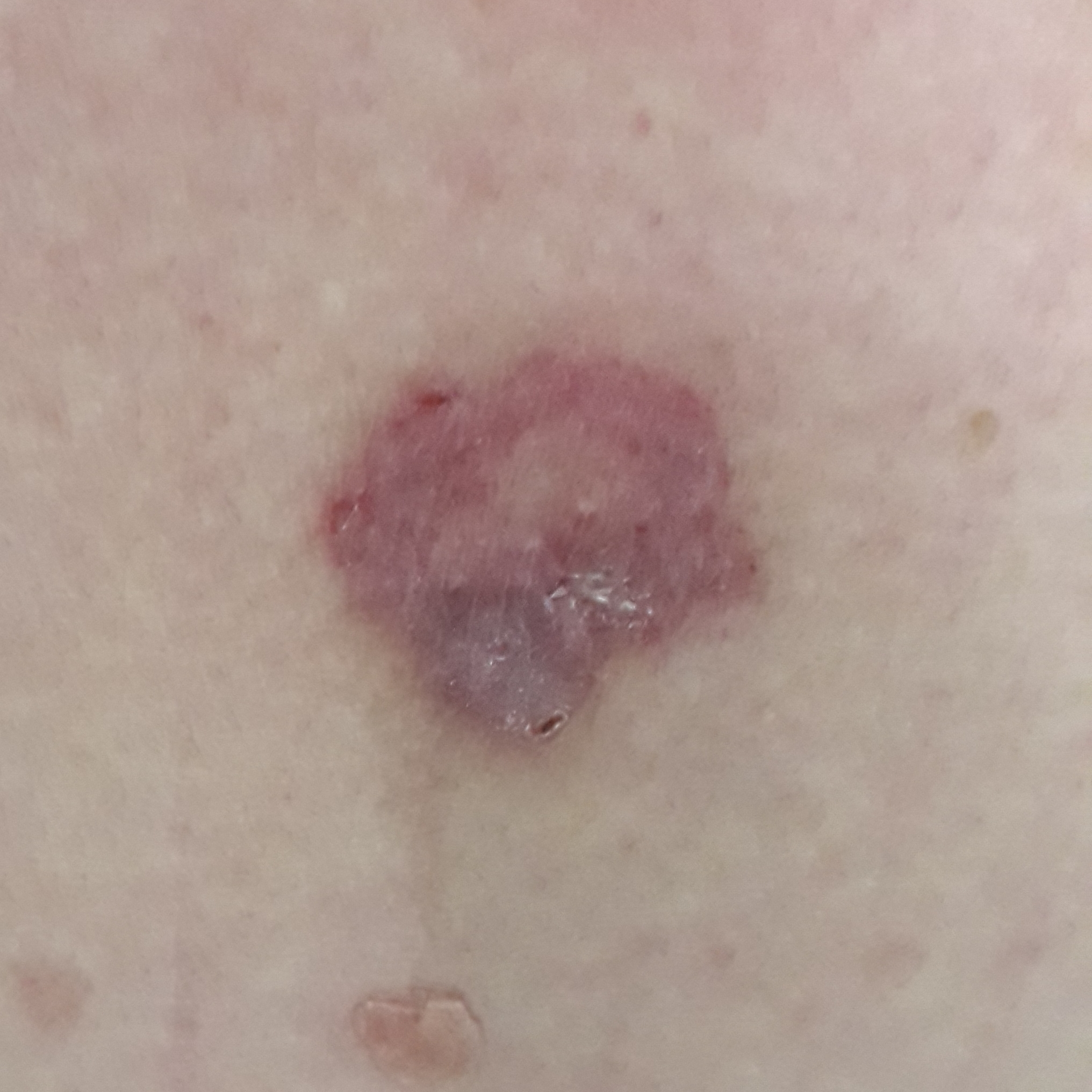exposures — prior skin cancer (patient or family) | skin type — II | image — smartphone clinical photo | subject — male, 50 years old | body site — the back | lesion size — approx. 23 × 21 mm | diagnostic label — basal cell carcinoma (biopsy-proven).